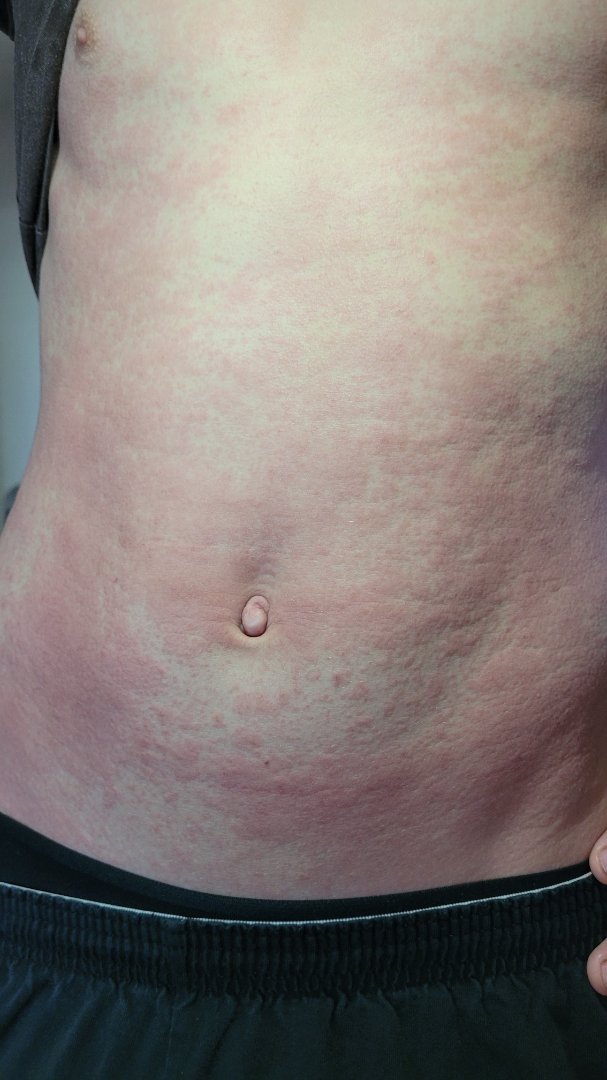The condition has been present for one to four weeks. This is a close-up image. Self-categorized by the patient as a rash. Reported lesion symptoms include burning and itching. The subject is a male aged 18–29. The leg, front of the torso, arm and back of the torso are involved. Viral Exanthem and Urticaria were considered with similar weight; less likely is Drug Rash.